Acquired for a research image collection, with no referral diagnosis; by self-report, a personal history of cancer; few moles overall by the patient's own estimate — 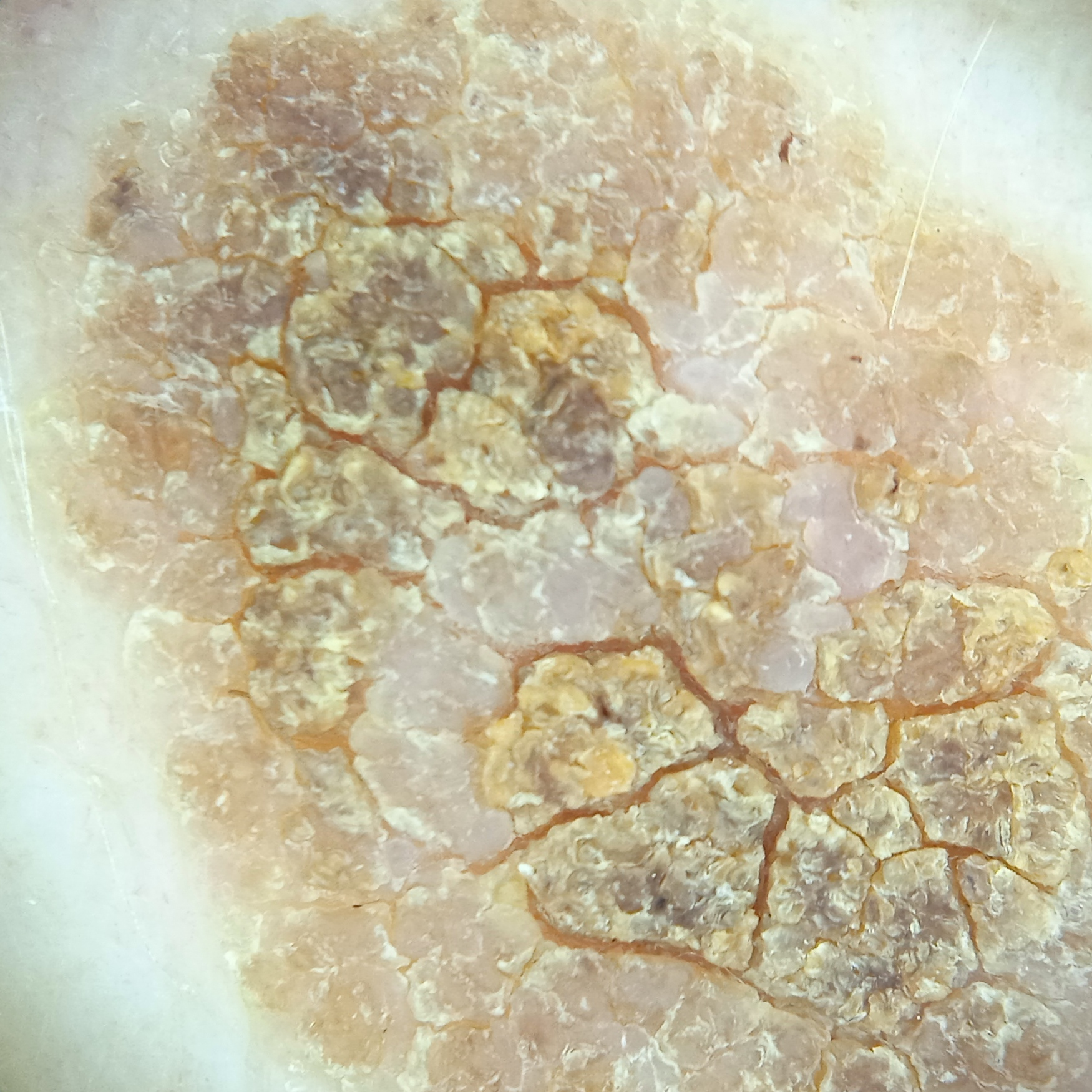{
  "lesion_location": "the back",
  "lesion_size": {
    "diameter_mm": 15.1
  },
  "diagnosis": {
    "name": "seborrheic keratosis",
    "malignancy": "benign"
  }
}